A close-up photograph. The subject is female. The lesion involves the leg — 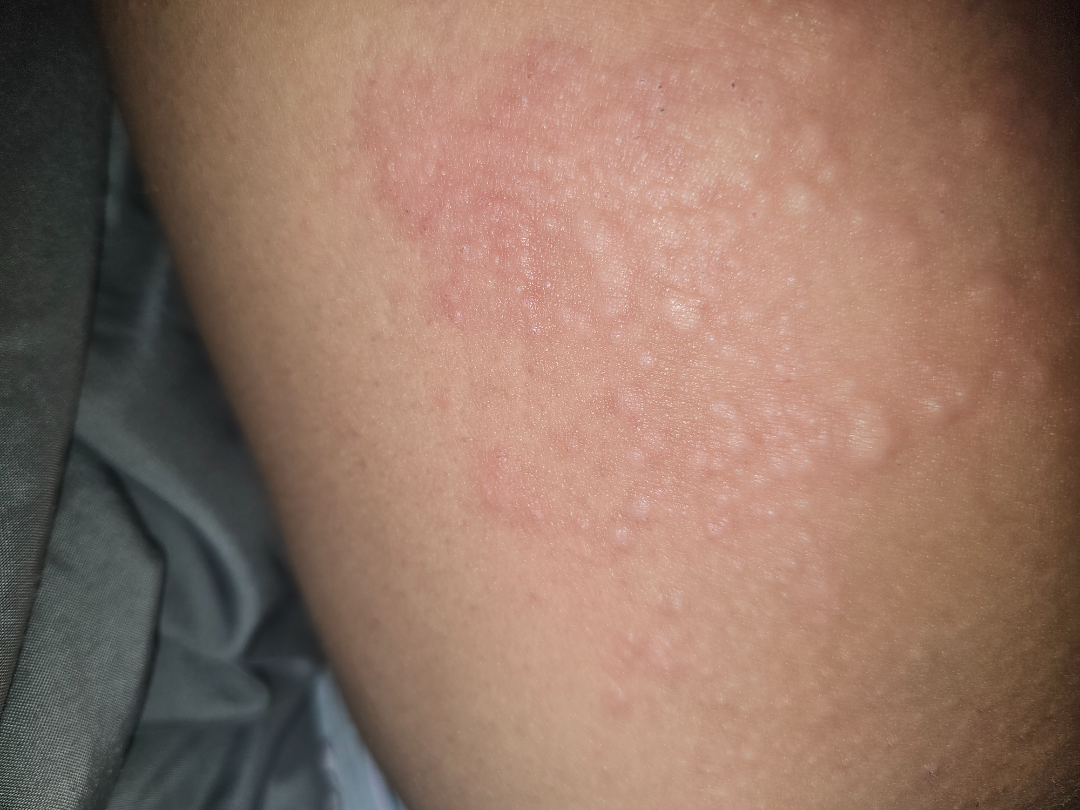Urticaria and Allergic Contact Dermatitis were each considered, in no particular order.